A close-up photograph, Fitzpatrick skin type III; non-clinician graders estimated Monk skin tone scale 1 or 2 (two reviewer pools), present for less than one week, the patient described the issue as a rash, the affected area is the leg: 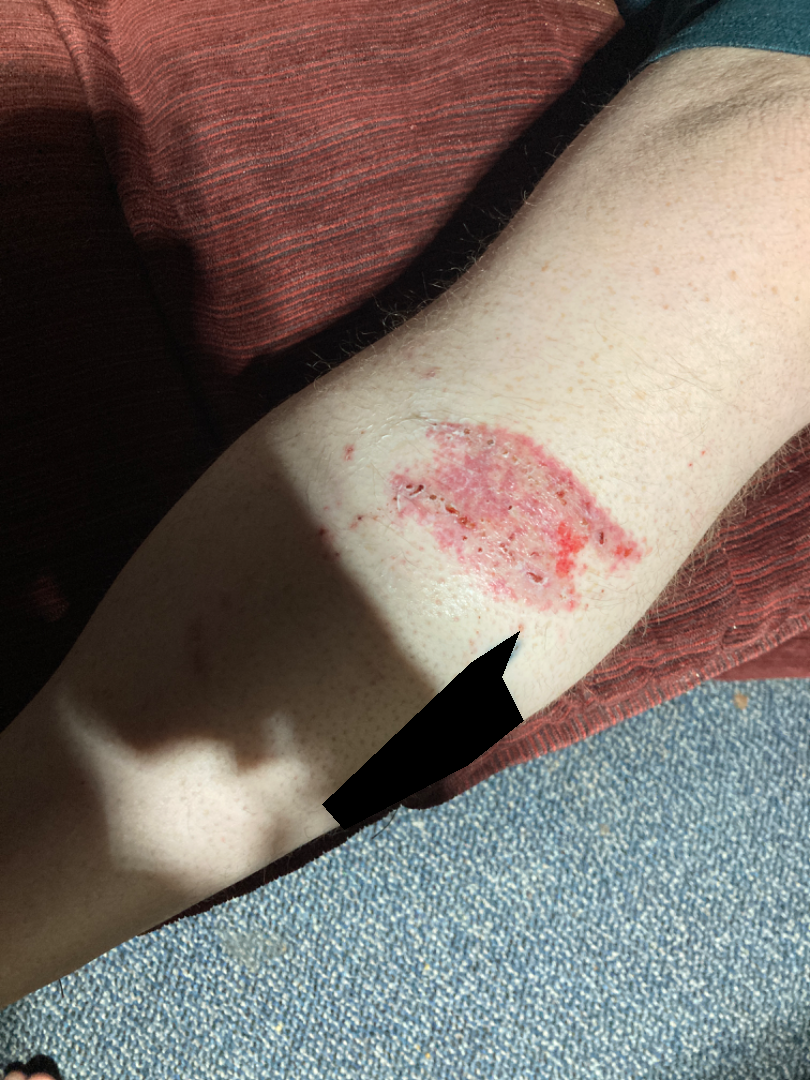The dermatologist could not determine a likely condition from the photograph alone.